Male patient, age 18–29; the photograph is a close-up of the affected area; the arm, head or neck and front of the torso are involved:
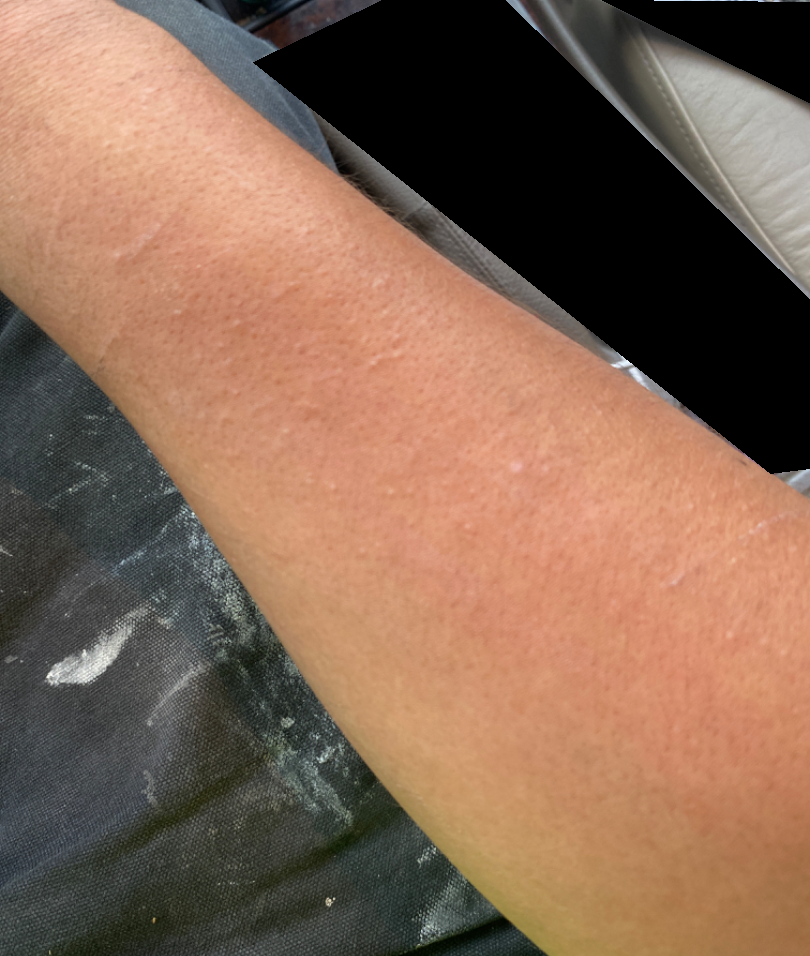| key | value |
|---|---|
| patient describes the issue as | a rash |
| skin tone | Fitzpatrick skin type II; non-clinician graders estimated Monk skin tone scale 4 (US pool) or 3 (India pool) |
| reported symptoms | itching, burning and darkening |
| texture | raised or bumpy |
| history | less than one week |
| associated systemic symptoms | mouth sores, chills and fatigue |
| impression | the leading consideration is Photodermatitis; an alternative is Urticaria; also consider Allergic Contact Dermatitis; less probable is Irritant Contact Dermatitis; lower on the differential is Eczema |